A dermoscopic photograph of a skin lesion: 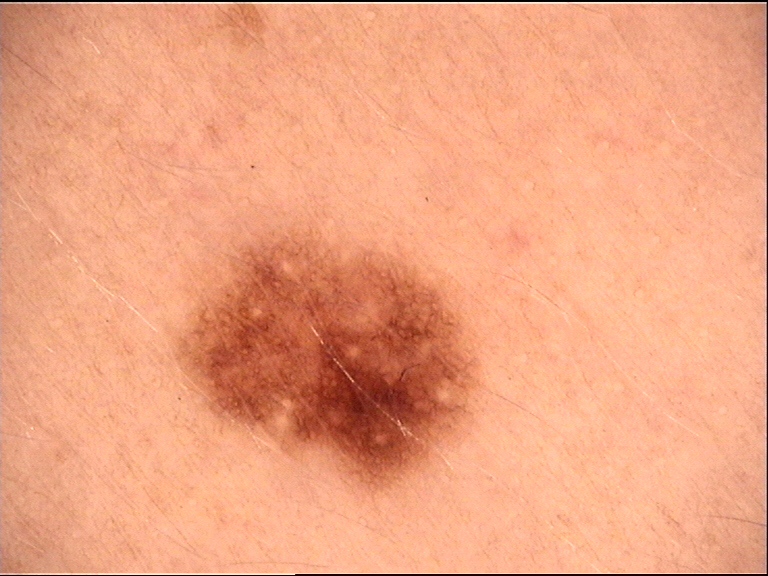Classified as a benign lesion — a dysplastic junctional nevus.